A close-up photograph — 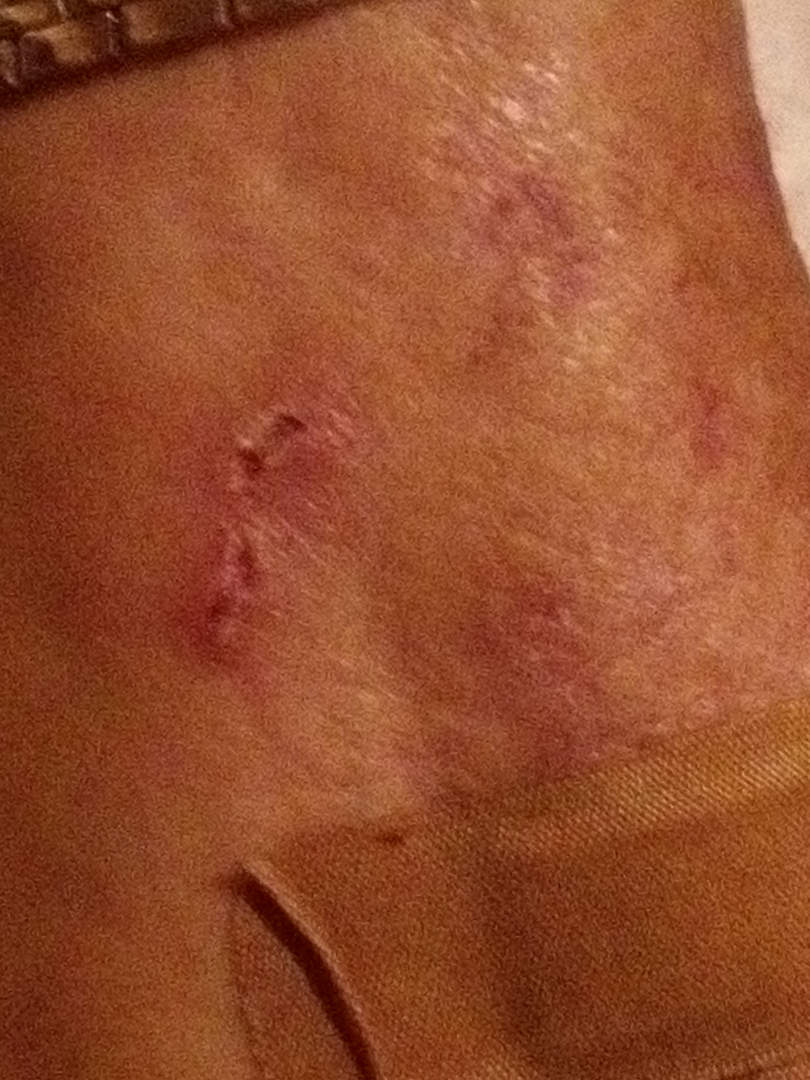The skin condition could not be confidently assessed from this image.